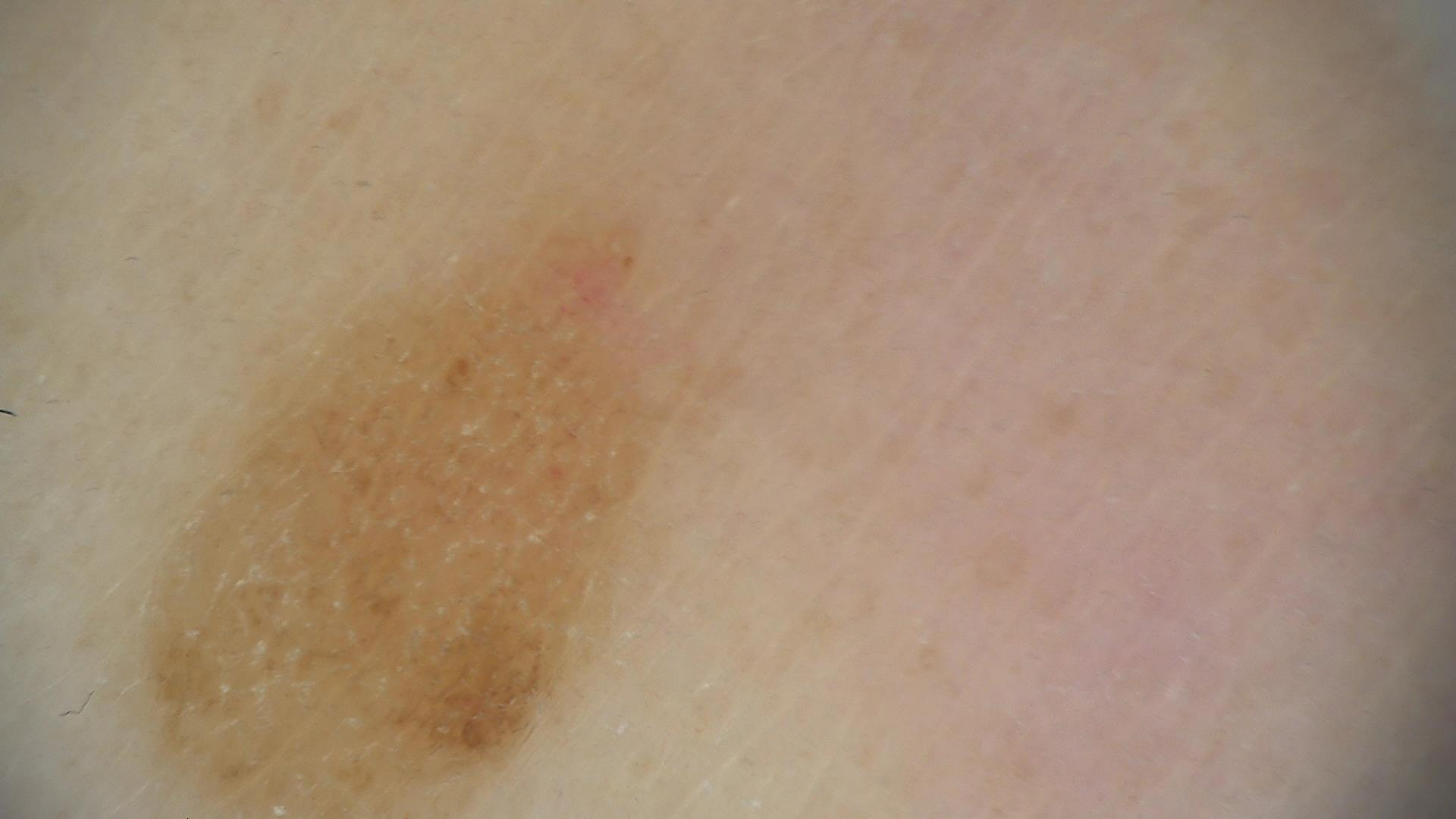modality: dermoscopy
class: dysplastic junctional nevus (expert consensus)